Fitzpatrick phototype II; human graders estimated Monk skin tone scale 1 or 2 · the photograph was taken at an angle — 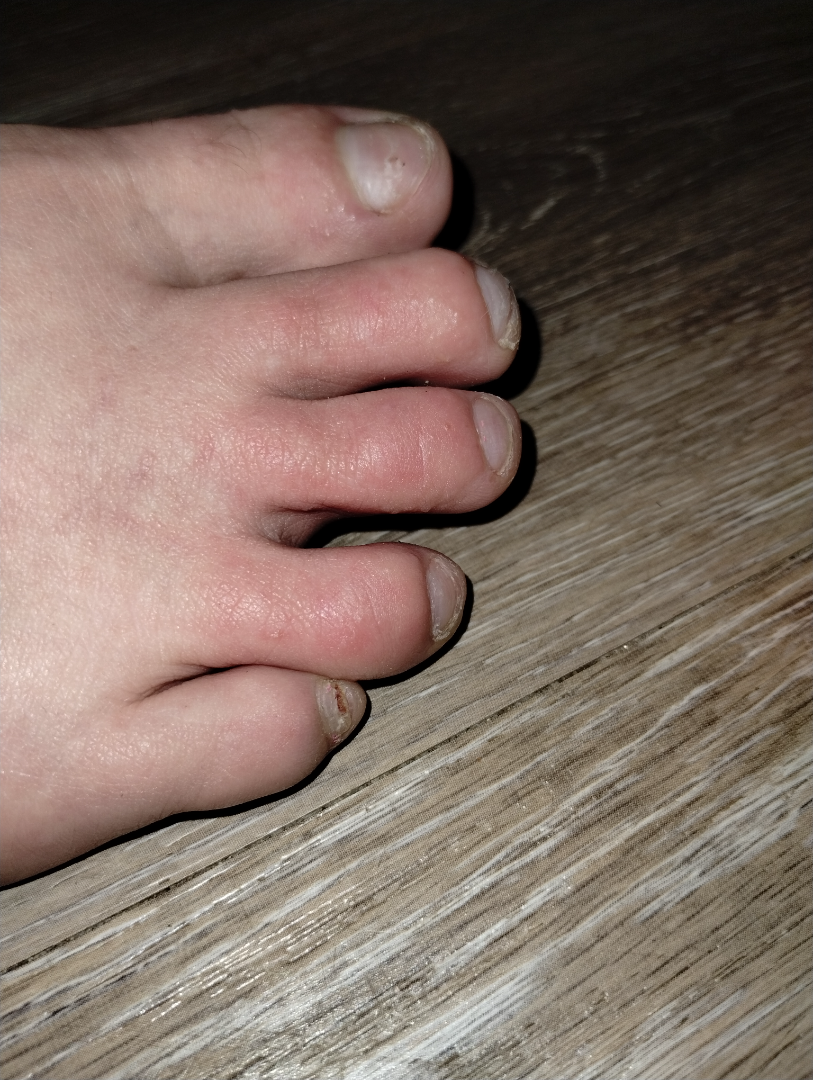The reviewing dermatologist did not identify a discernible skin condition.